Collected as part of a research study, without a referral diagnosis; a female patient age 60; the patient describes having few moles overall.
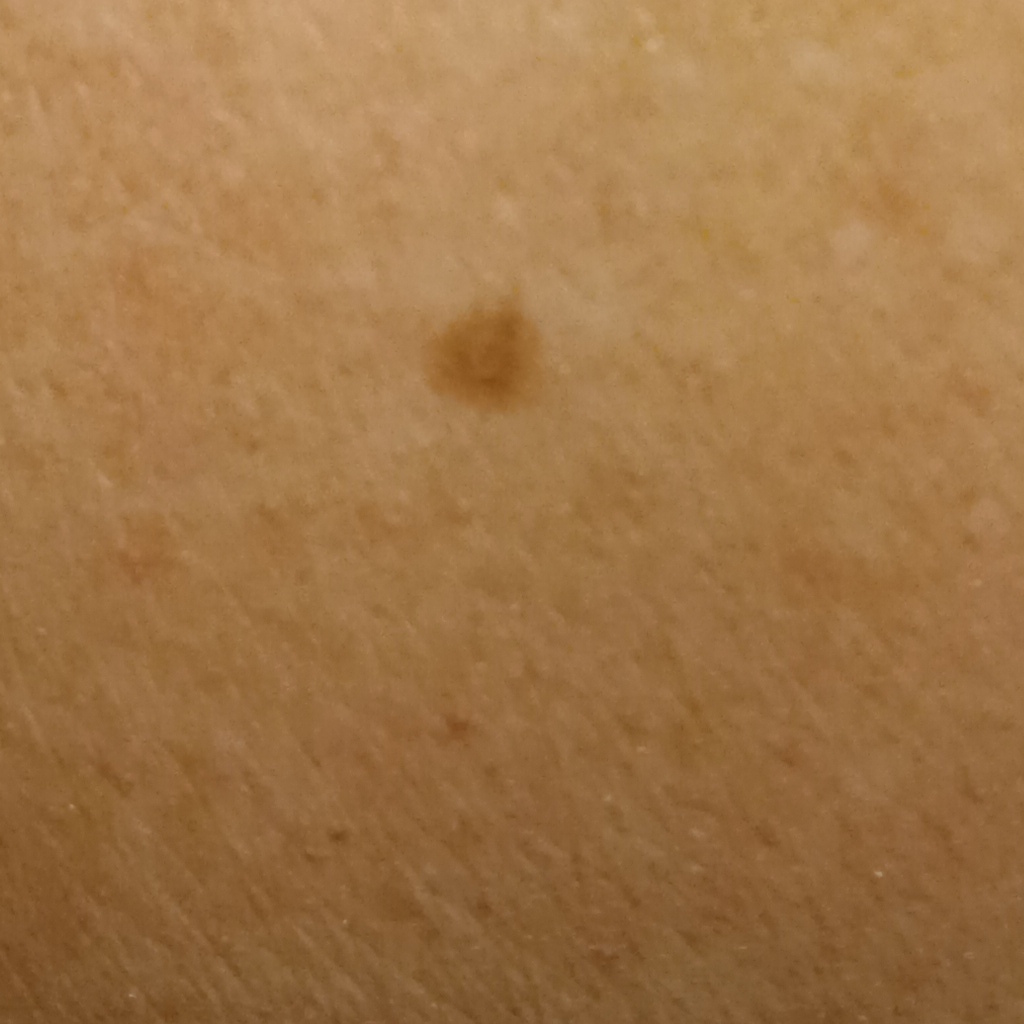* anatomic site · an arm
* diagnostic label · melanocytic nevus (dermatologist consensus)